The patient was assessed as Fitzpatrick II · a male subject aged approximately 80 · a skin lesion imaged with contact-polarized dermoscopy — 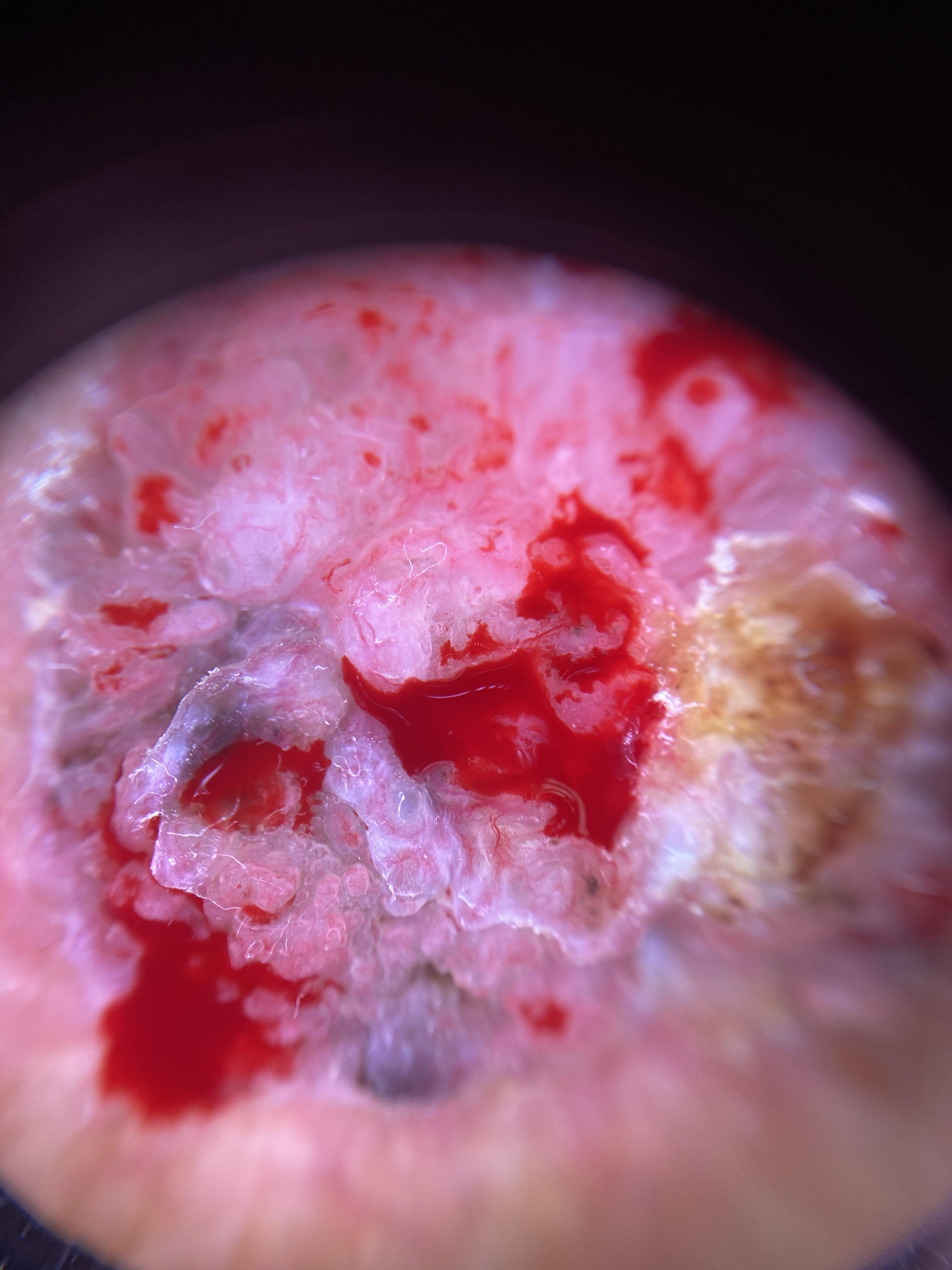Located on the trunk. Confirmed on histopathology as a lesion of adnexal (follicular) origin — a basal cell carcinoma.